A dermatoscopic image of a skin lesion.
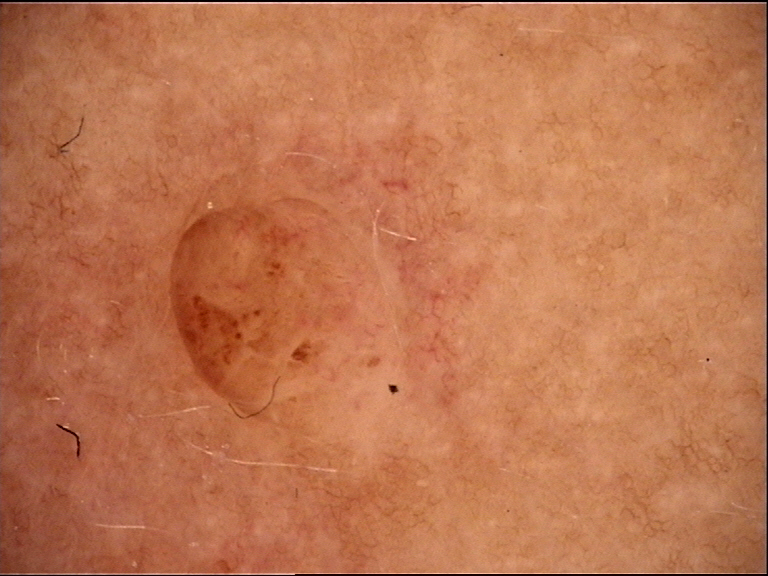This is a banal lesion. Consistent with a dermal nevus.